A skin lesion imaged with a dermatoscope. A female patient, aged approximately 30 — 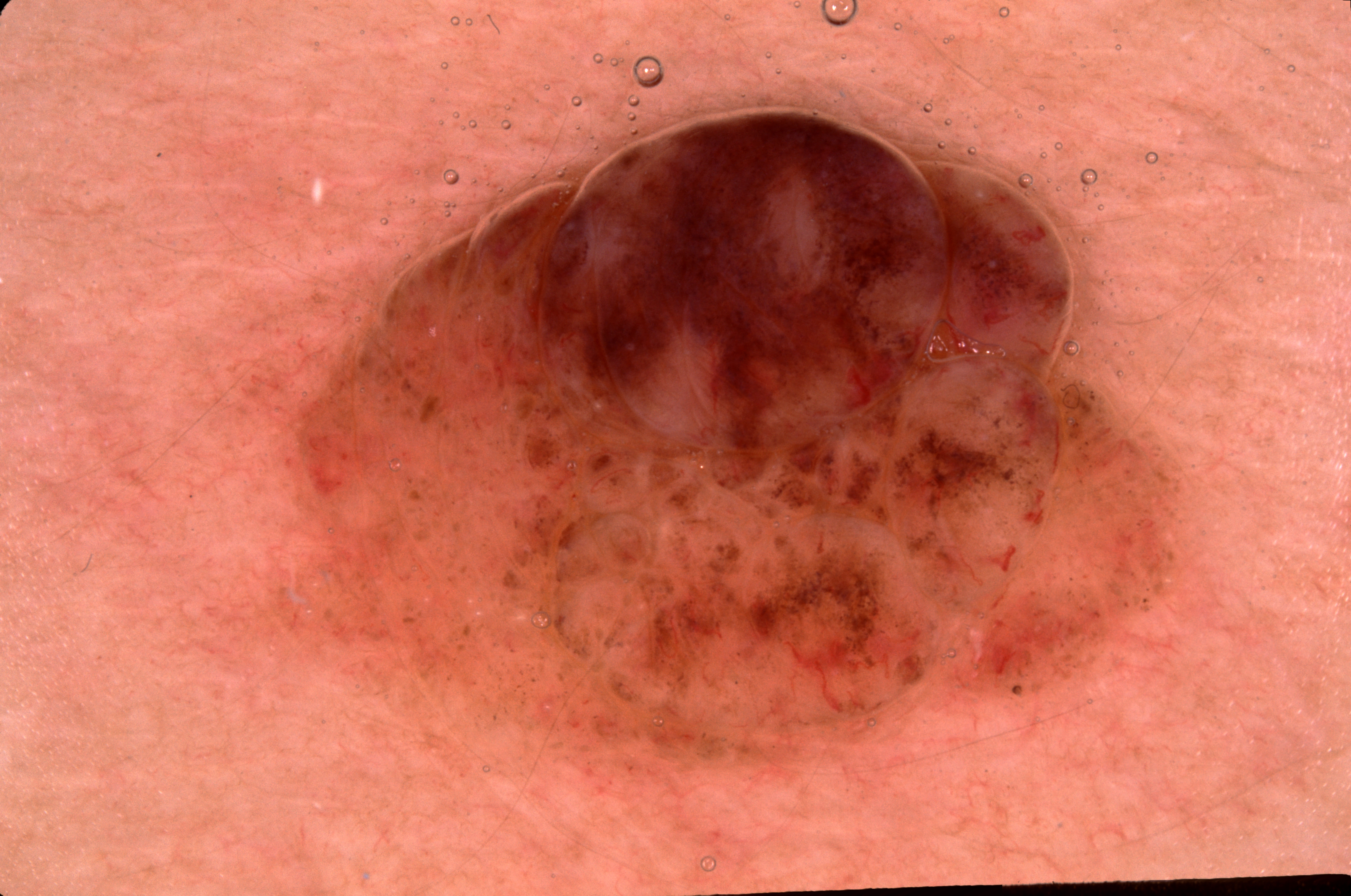The lesion takes up a large portion of the image. Dermoscopic assessment notes milia-like cysts, with no streaks, negative network, or pigment network. The lesion's extent is [189, 51, 1201, 885]. The clinical diagnosis was a melanocytic nevus, a benign skin lesion.